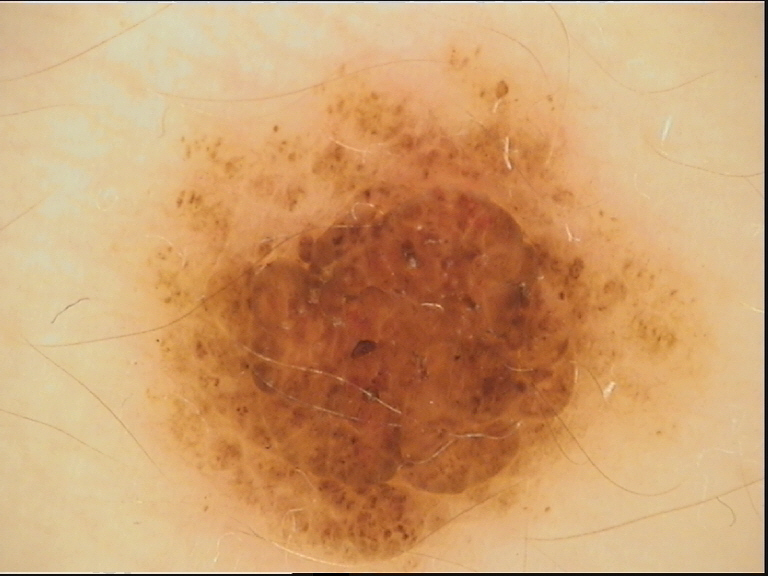Labeled as a compound nevus.